The lesion is described as raised or bumpy · female contributor, age 50–59 · the affected area is the palm · no relevant systemic symptoms · the lesion is associated with bothersome appearance · close-up view.
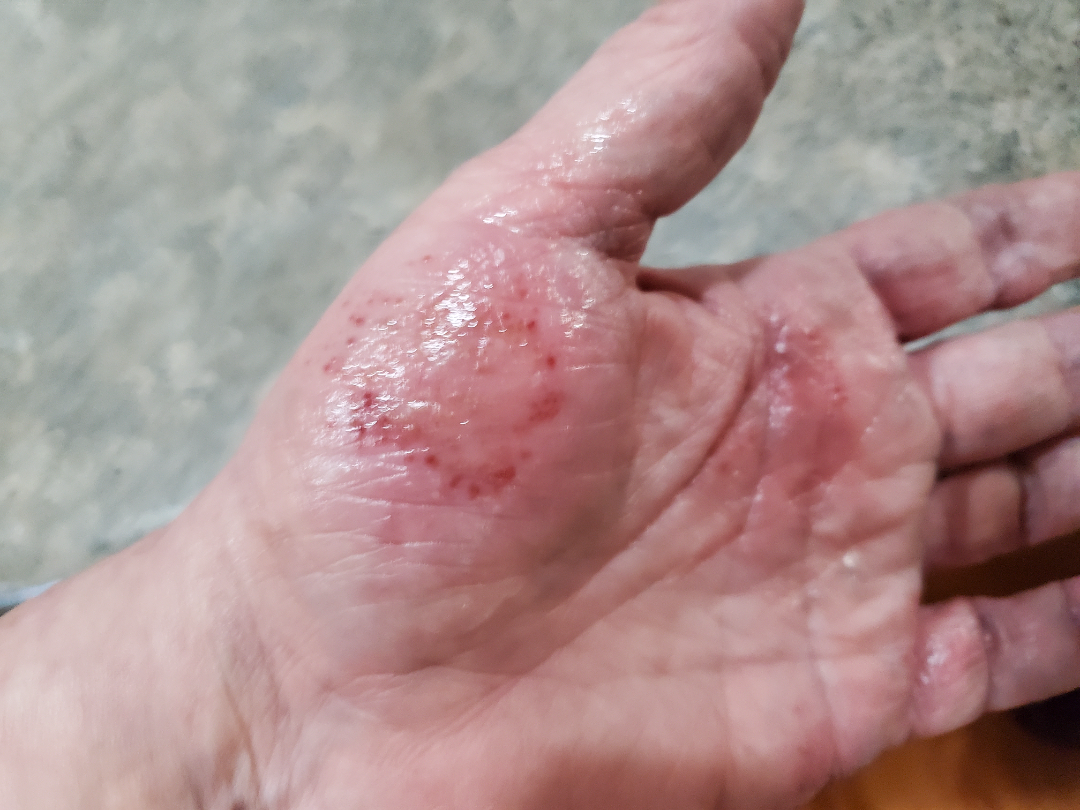Impression:
Abrasion, scrape, or scab; Burn of skin; and Eczema were considered with similar weight.